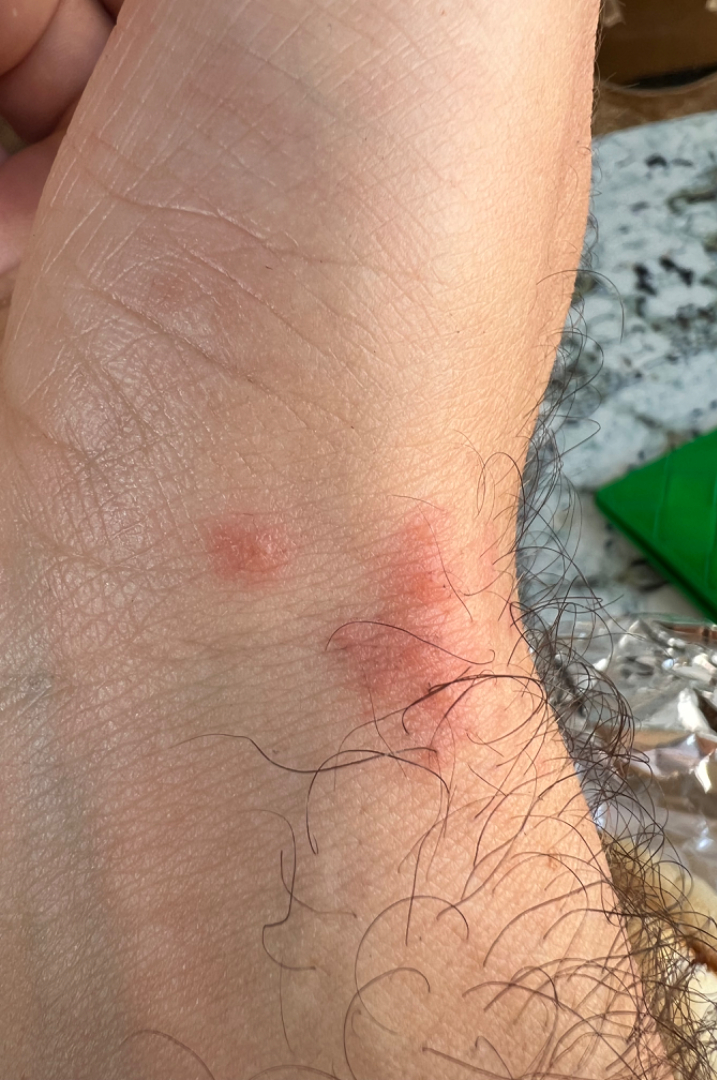Patient information:
The patient reports the condition has been present for about one day. The affected area is the arm. Symptoms reported: burning. Fitzpatrick phototype III. The lesion is described as raised or bumpy. A close-up photograph. The patient described the issue as a rash. No constitutional symptoms were reported.
Review:
The primary impression is Insect Bite; also raised was Eczema; a more distant consideration is Allergic Contact Dermatitis.